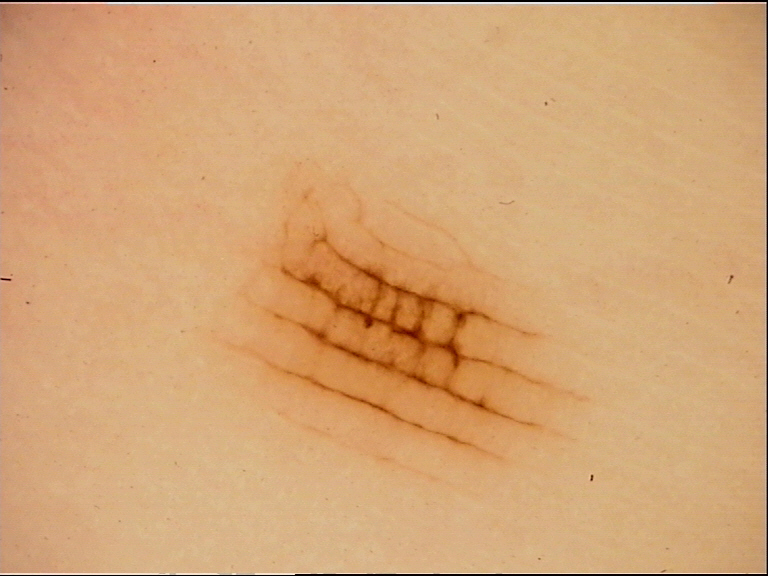- label: acral junctional nevus (expert consensus)